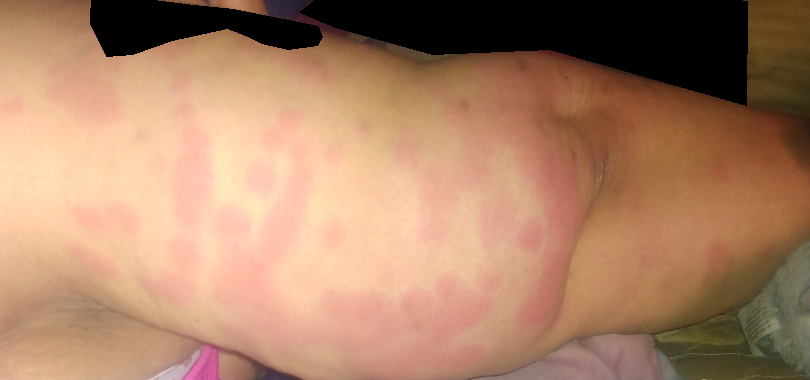History:
The patient is a female aged 40–49. The patient reports the condition has been present for less than one week. Reported lesion symptoms include burning, enlargement and itching. The palm, arm and head or neck are involved. The photo was captured at a distance. Fitzpatrick skin type IV; non-clinician graders estimated 3 on the Monk skin tone scale. The patient considered this a rash. Texture is reported as raised or bumpy.
Impression:
On remote review of the image: the primary impression is Urticaria; also consider Leukocytoclastic Vasculitis; less likely is Insect Bite.